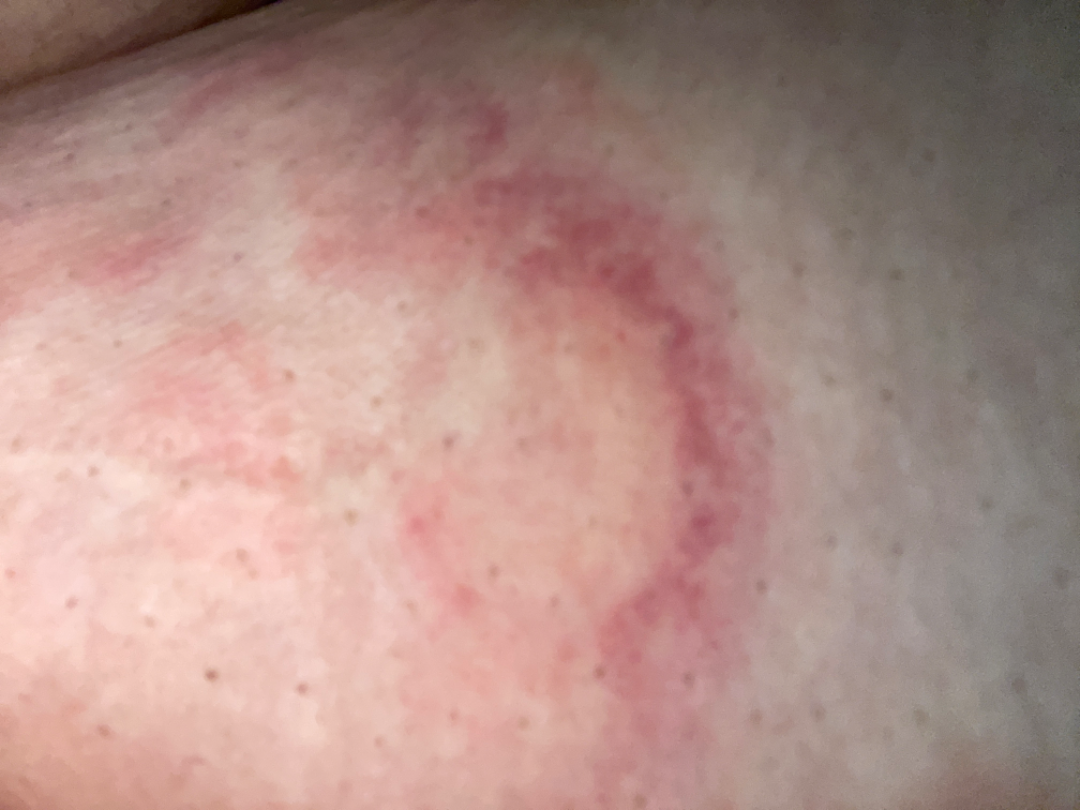The condition could not be reliably identified from the image. The subject is female. The patient reports enlargement and itching. Present for one to four weeks. Located on the front of the torso. The patient described the issue as a rash. No relevant systemic symptoms. This is a close-up image. The patient reports the lesion is raised or bumpy.